A dermoscopy image of a single skin lesion:
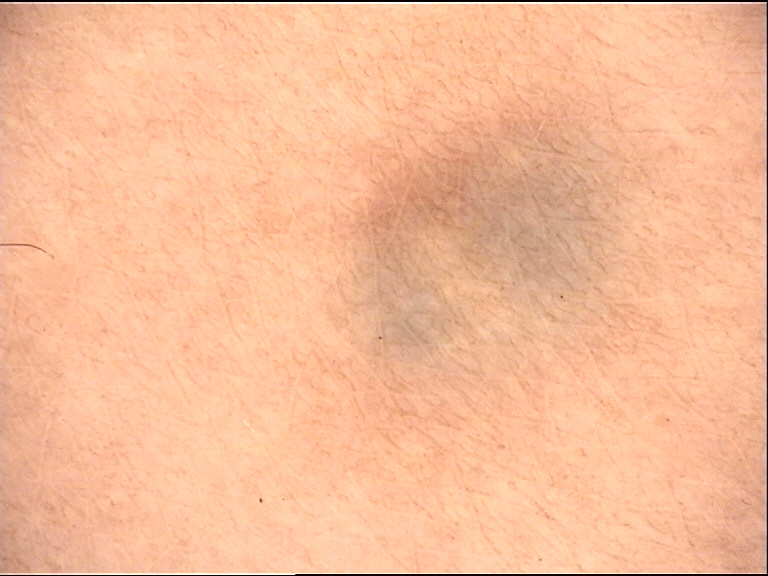Impression:
Classified as a dermal lesion — a blue nevus.